Dermoscopy of a skin lesion.
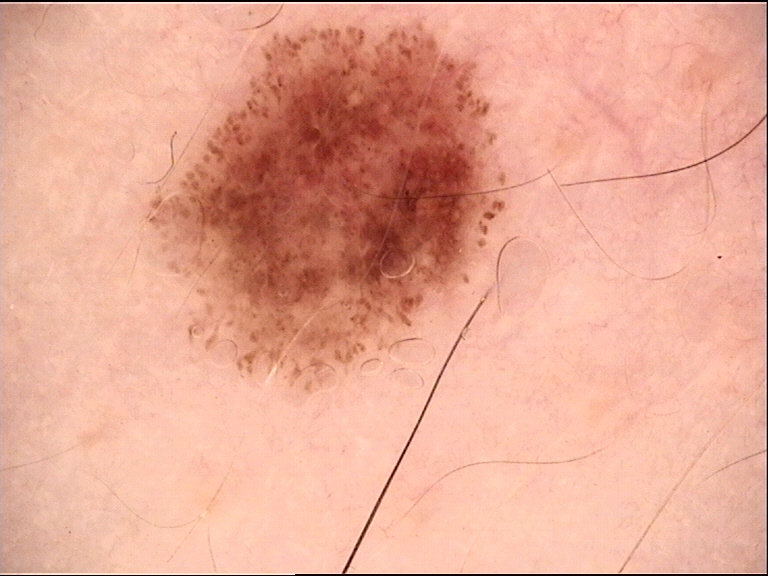Impression:
Diagnosed as a dysplastic junctional nevus.